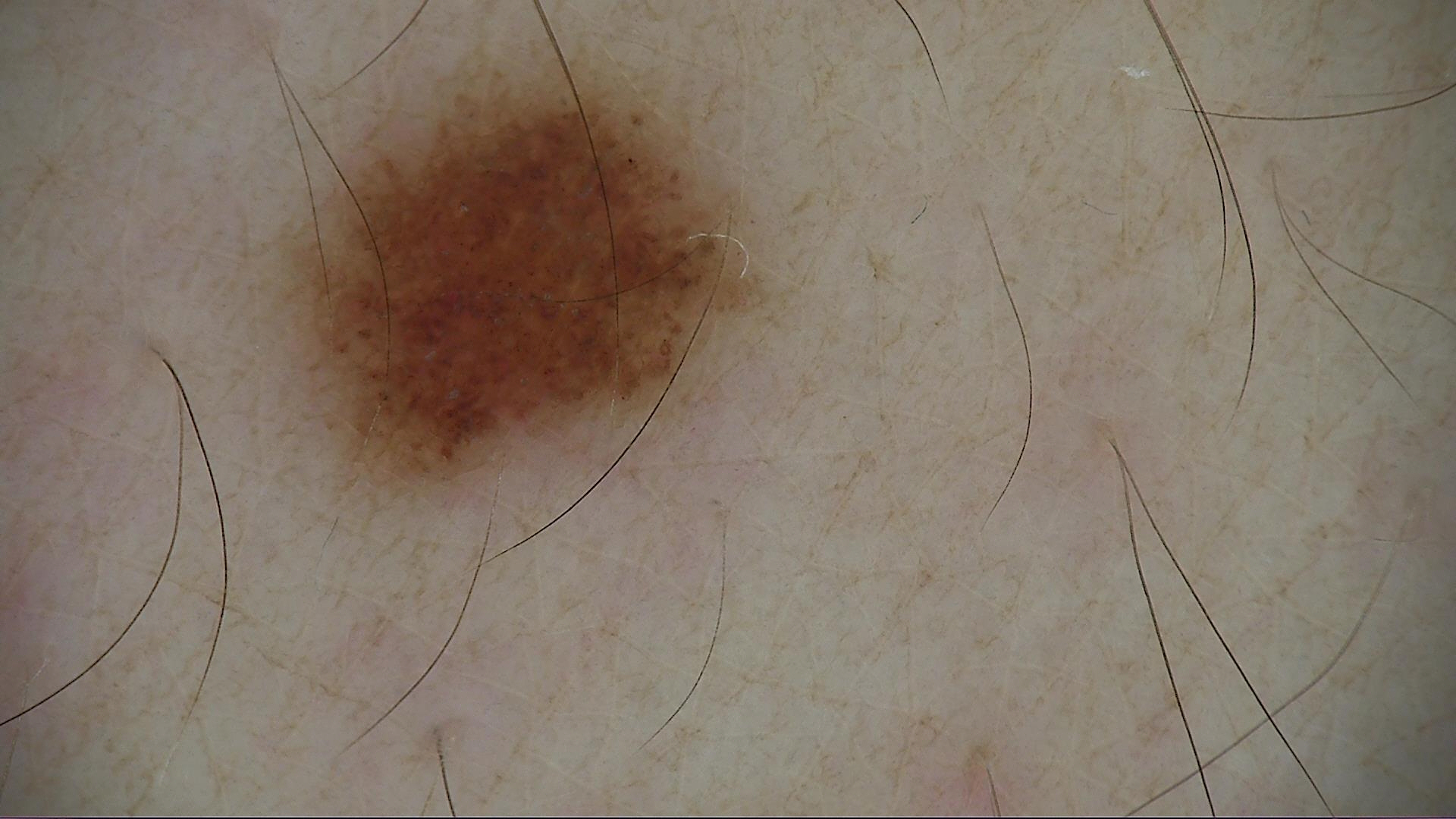A dermoscopic close-up of a skin lesion. Labeled as a dysplastic junctional nevus.